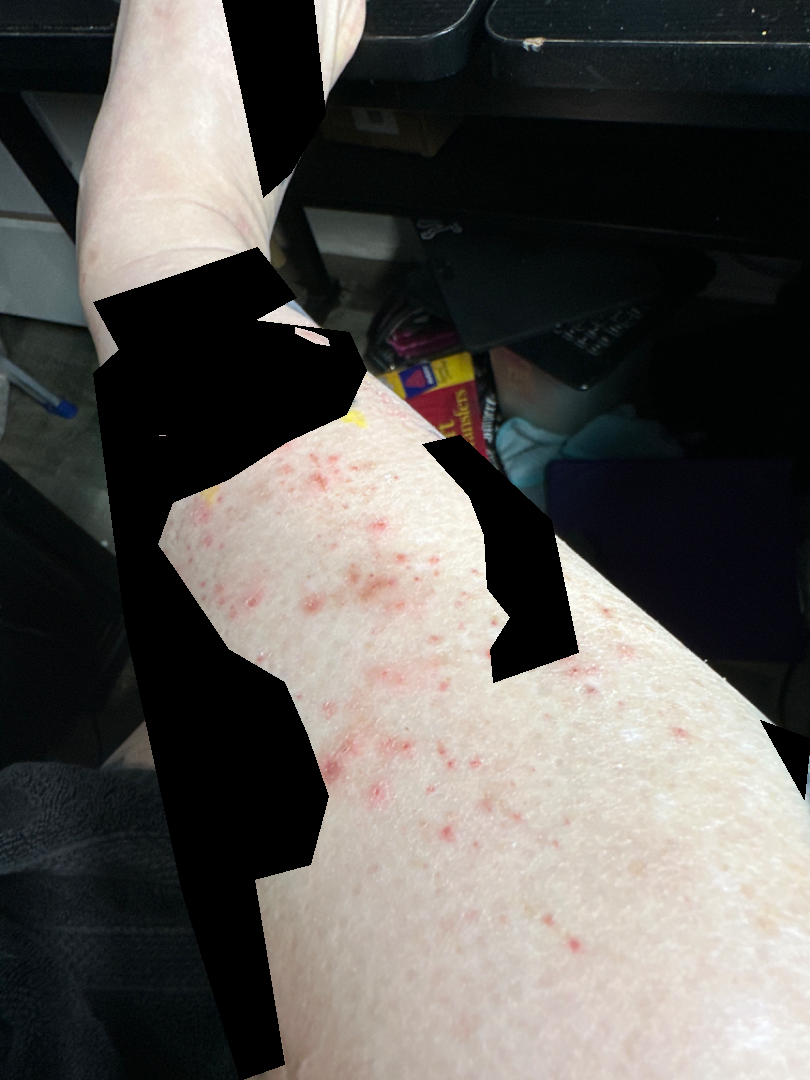The lesion involves the leg. This image was taken at an angle. Female subject, age 40–49. On remote review of the image, the primary impression is Pigmented purpuric eruption; an alternative is Leukocytoclastic Vasculitis.